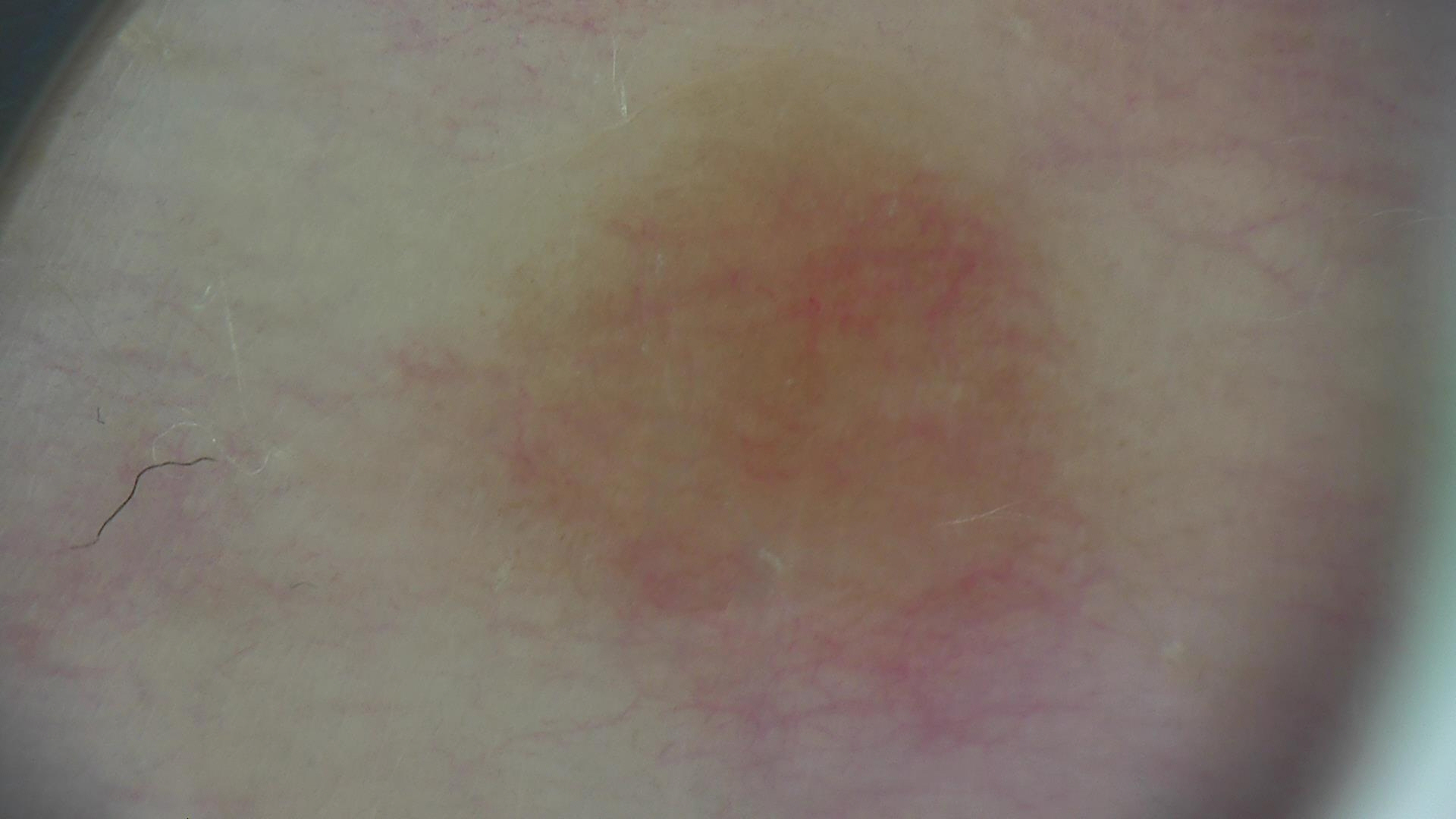{"image": "dermatoscopy", "lesion_type": {"main_class": "banal", "pattern": "junctional"}, "diagnosis": {"name": "junctional nevus", "code": "jb", "malignancy": "benign", "super_class": "melanocytic", "confirmation": "expert consensus"}}